The patient says their skin tans without first burning · a female patient age 60 · a dermoscopy image of a skin lesion · on a questionnaire the patient reported a personal history of skin cancer and a personal history of cancer — 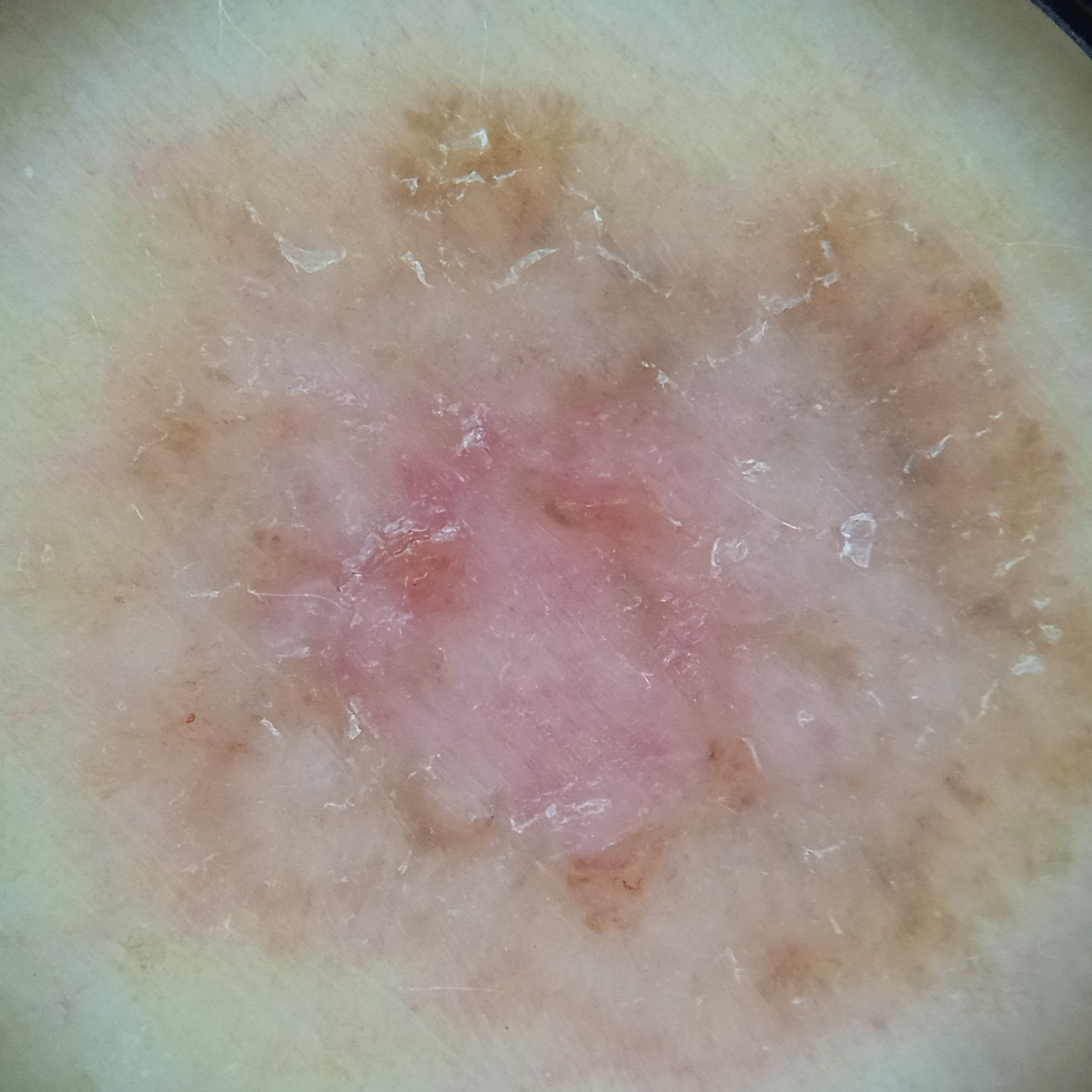Q: What is the anatomic site?
A: the torso
Q: Lesion size?
A: 13.2 mm
Q: What was the diagnosis?
A: basal cell carcinoma (dermatologist consensus)